The lesion involves the arm; the subject is 18–29, male; this image was taken at a distance:
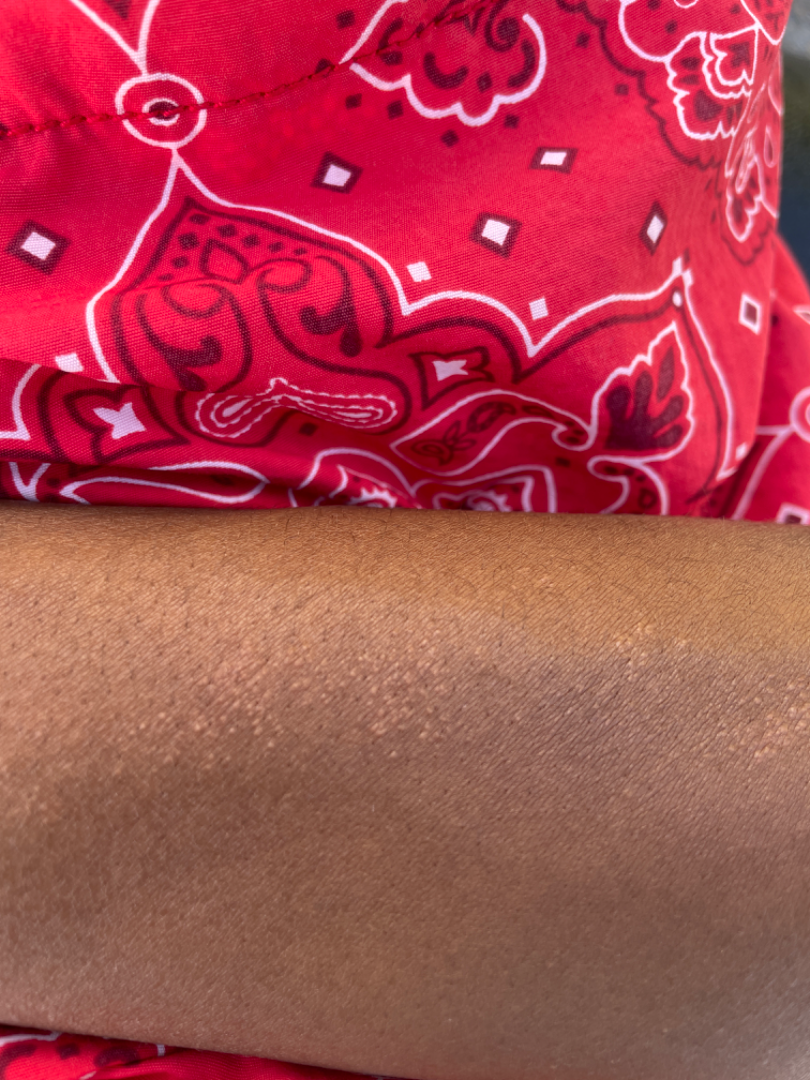| field | value |
|---|---|
| assessment | indeterminate |
| lesion texture | raised or bumpy |
| other reported symptoms | none reported |
| history | one to four weeks |
| self-categorized as | a rash |